A skin lesion imaged with a dermatoscope.
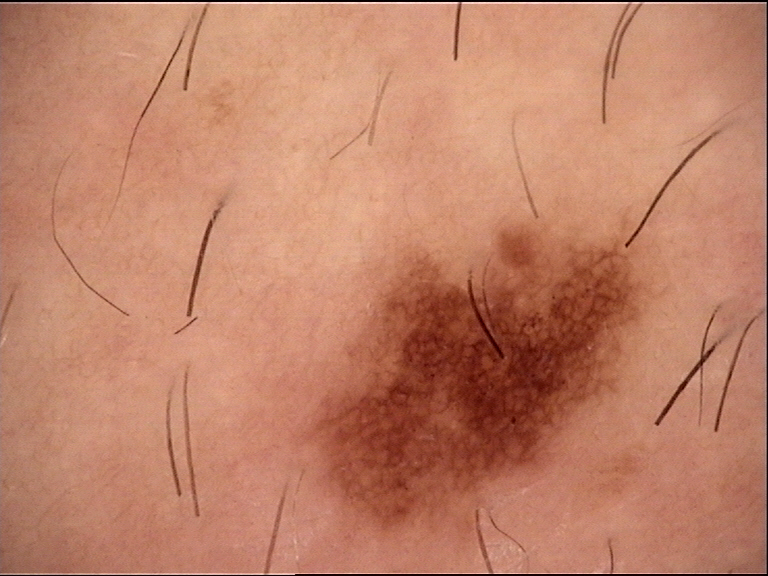diagnosis=dysplastic junctional nevus (expert consensus).